Male contributor, age 30–39 · the arm, back of the hand, top or side of the foot and palm are involved · an image taken at a distance: 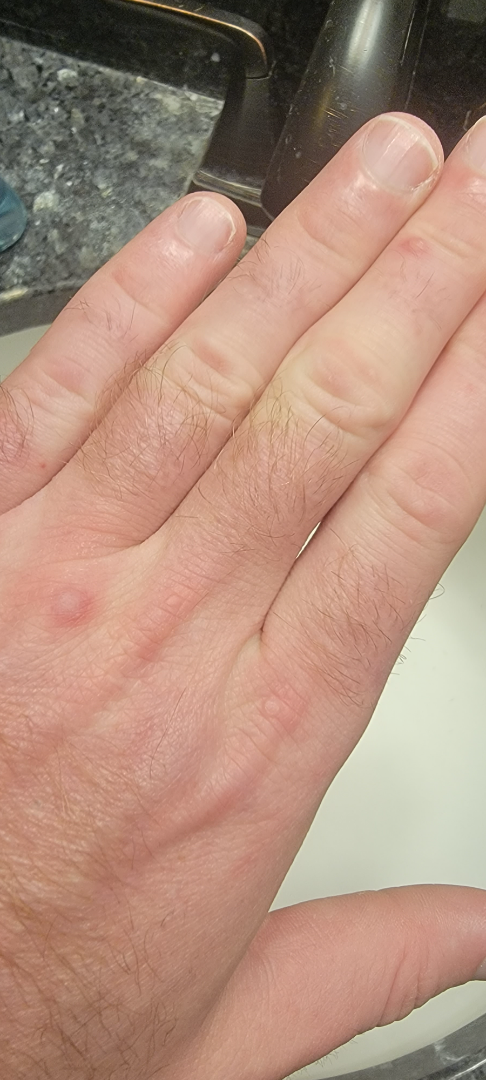Findings:
- present for: about one day
- described texture: raised or bumpy and fluid-filled
- systemic symptoms: fever
- reported symptoms: itching
- clinical impression: Psoriasis and Insect Bite were each considered, in no particular order; less likely is Folliculitis; lower on the differential is Dermatitis herpetiformis; a more distant consideration is Acute dermatitis, NOS; less probable is Skin and soft tissue atypical mycobacterial infection; a remote consideration is Perforating dermatosis